This is a close-up image: 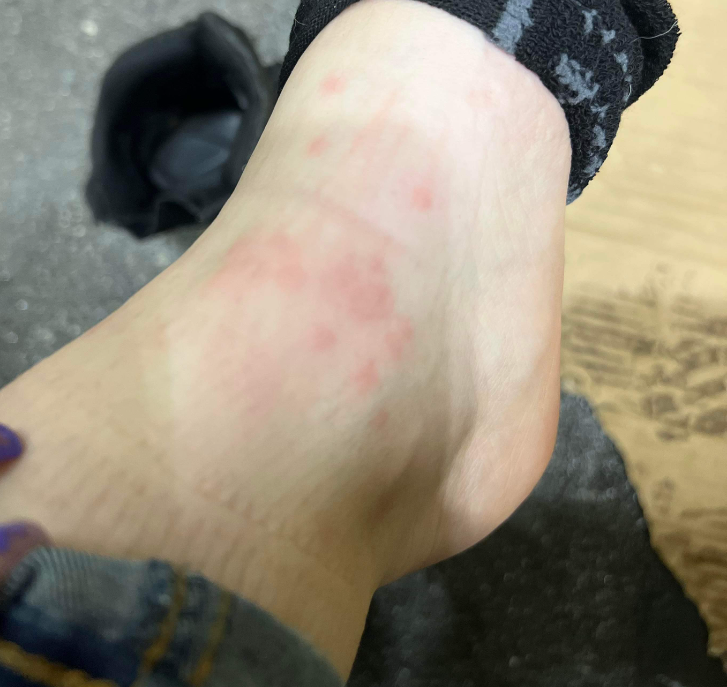The dermatologist could not determine a likely condition from the photograph alone.